A clinical close-up photograph of a skin lesion · by history, alcohol use, prior malignancy (patient or family), and tobacco use · the patient is Fitzpatrick phototype II — 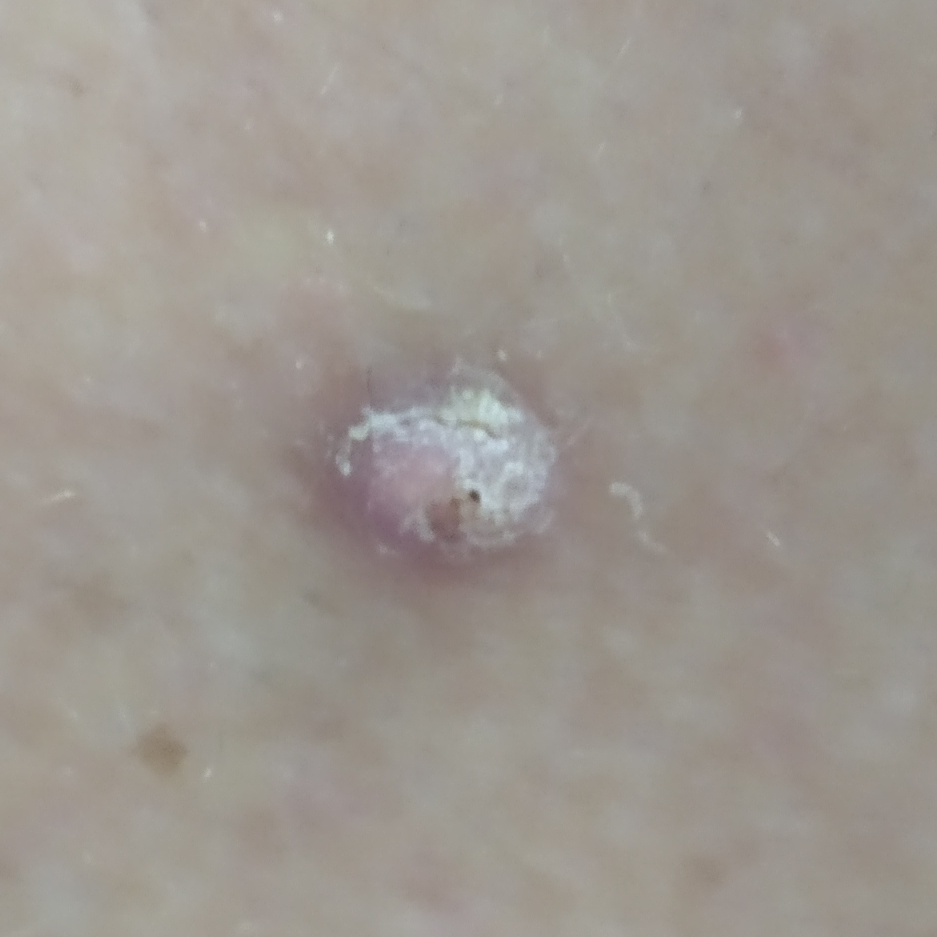The lesion is located on the back. The patient reports that the lesion is elevated. Biopsy-confirmed as a skin cancer — a squamous cell carcinoma.